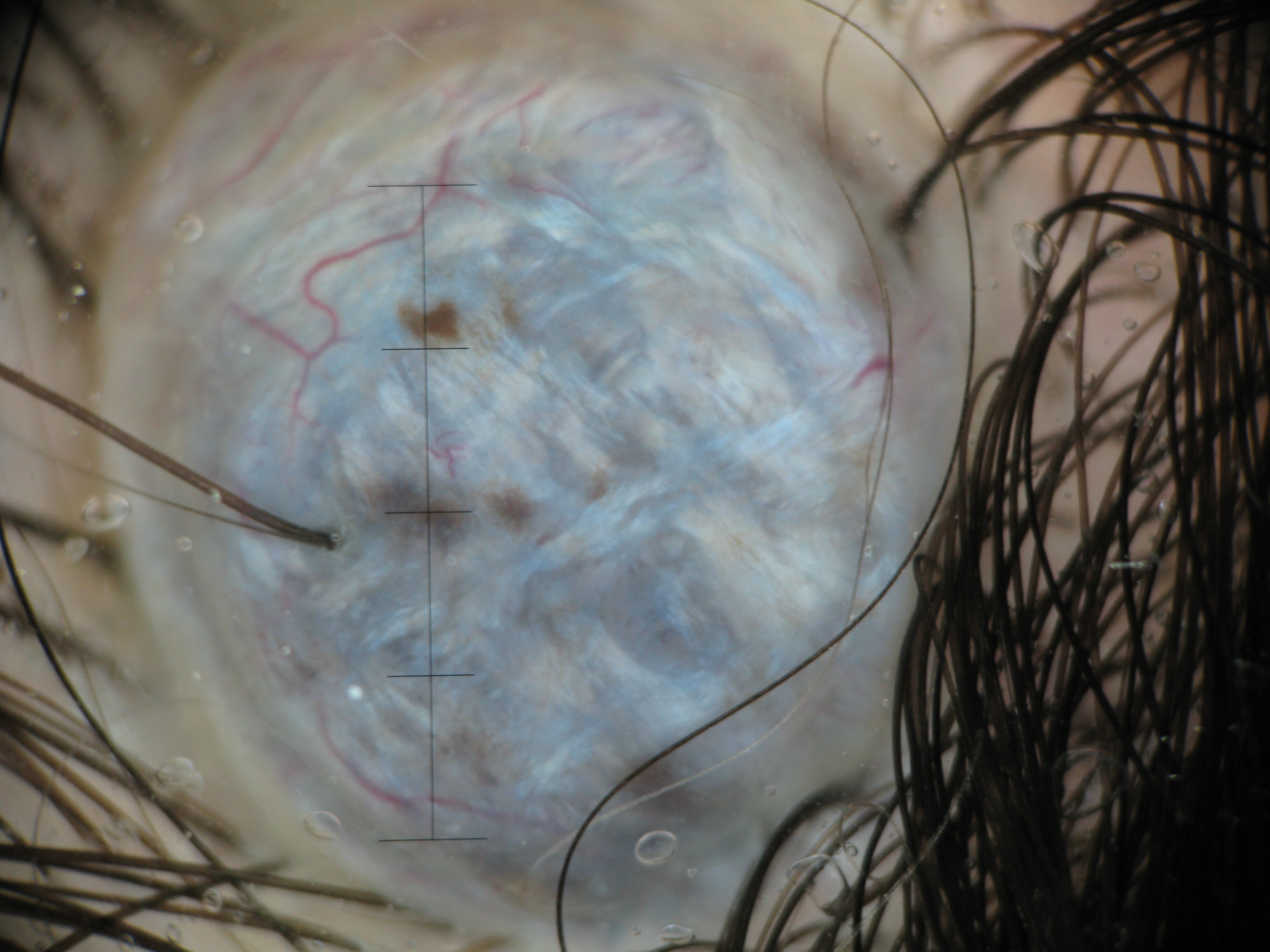Findings:
A dermoscopy image of a single skin lesion. The architecture is that of a banal, dermal lesion.
Conclusion:
Labeled as a blue nevus.